A smartphone photograph of a skin lesion; the patient is Fitzpatrick skin type II; a female patient in their 60s; the chart notes prior skin cancer (patient or family), tobacco use, and prior malignancy (patient or family).
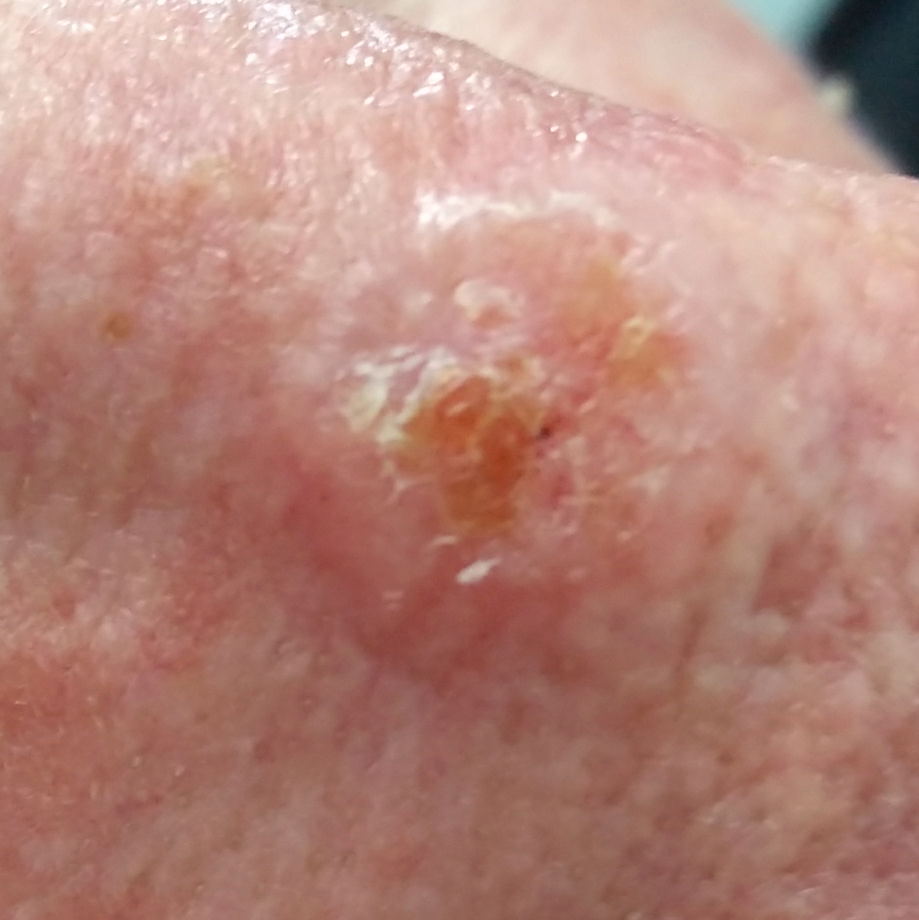Patient and lesion: The lesion is located on the nose. The patient describes that the lesion hurts, itches, has bled, has grown, and is elevated, but has not changed. Conclusion: Biopsy-confirmed as a malignant lesion — a basal cell carcinoma.